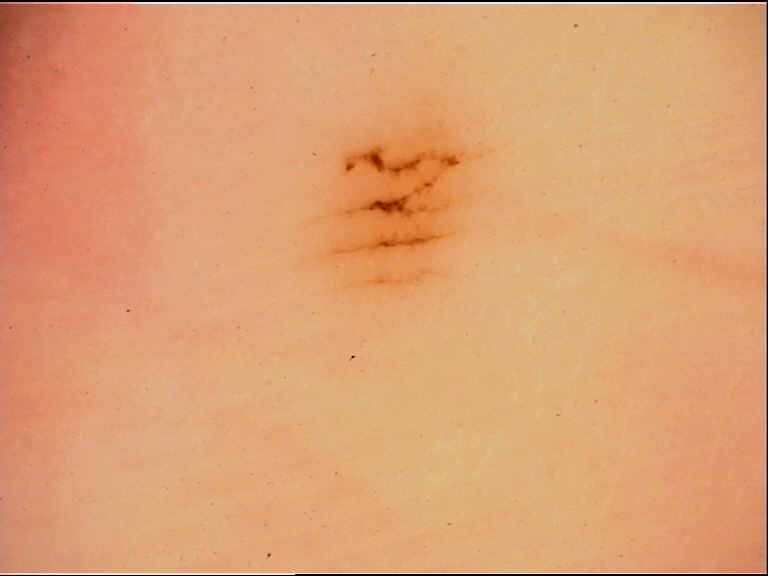Impression:
The diagnostic label was an acral junctional nevus.